Present for one to four weeks · the subject is male · the contributor notes the lesion is fluid-filled · Fitzpatrick phototype IV; lay graders estimated 3 on the MST · the photograph is a close-up of the affected area · the patient described the issue as a rash · the affected area is the arm:
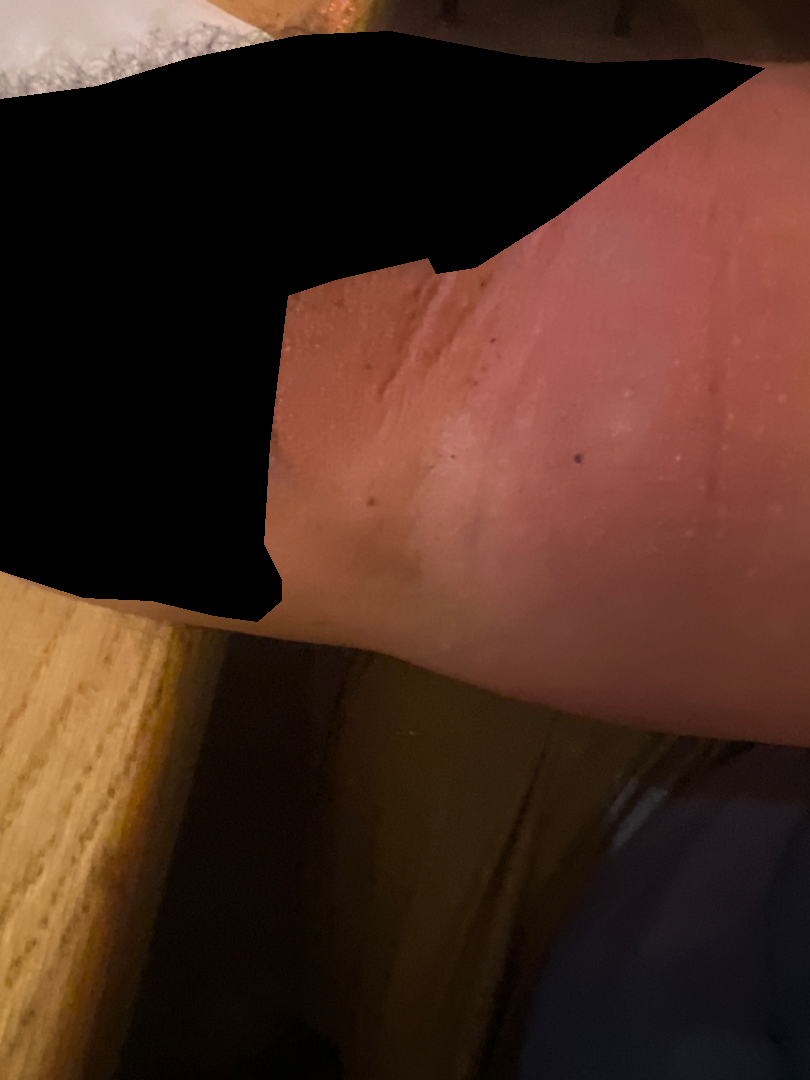Review: Cellulitis, Eczema and Allergic Contact Dermatitis were each considered, in no particular order.